This image was taken at a distance · the contributor is a female aged 40–49 · the affected area is the head or neck, back of the torso, arm, top or side of the foot, leg and back of the hand.
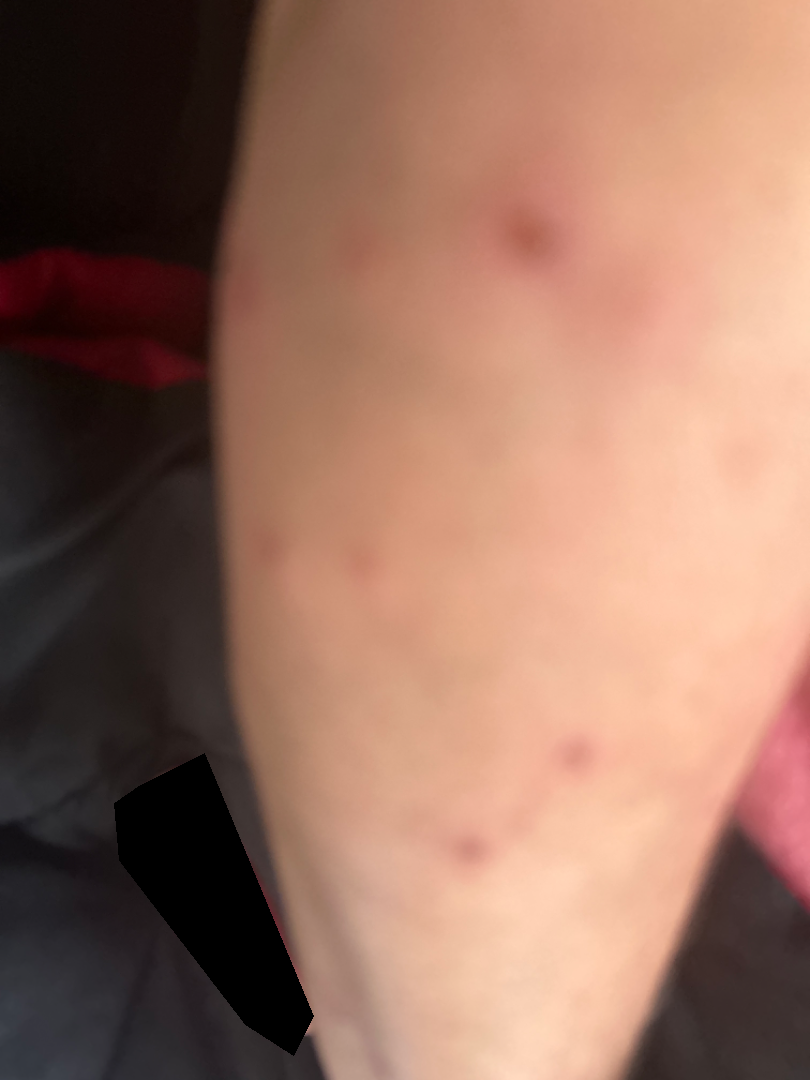The condition could not be reliably identified from the image.